The back of the hand is involved, this is a close-up image — 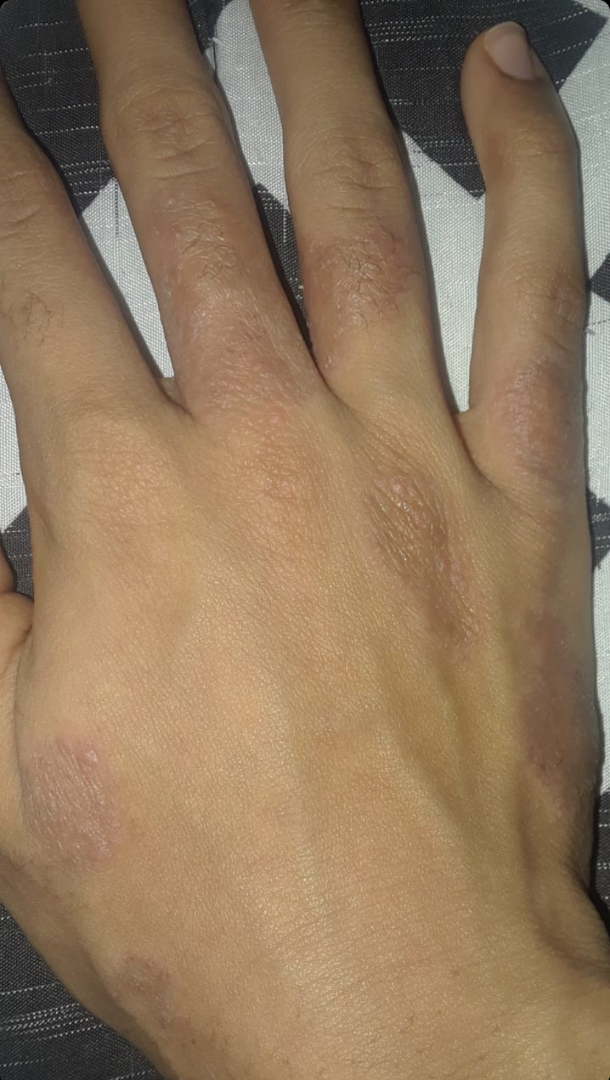History: The patient considered this a rash. The patient indicates the lesion is rough or flaky. No associated systemic symptoms reported. Reported lesion symptoms include burning, itching and bothersome appearance. Reported duration is one to four weeks. Impression: On remote review of the image: Eczema and Lichen planus/lichenoid eruption were considered with similar weight; lower on the differential is Irritant Contact Dermatitis.